The subject is a female aged 50–59 · the contributor notes enlargement and bothersome appearance · reported duration is more than one year · the leg is involved · the lesion is described as rough or flaky · self-categorized by the patient as a rash · no constitutional symptoms were reported · close-up view · Fitzpatrick skin type I.
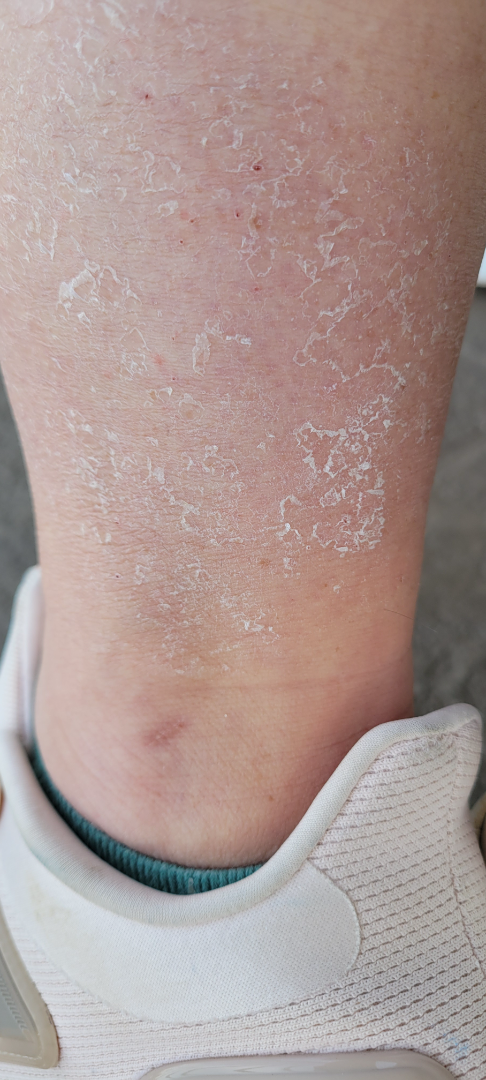differential = a single dermatologist reviewed the case: the favored diagnosis is Xerosis; with consideration of Eczema; less likely is post-sunburn peeling/superficial desquamation